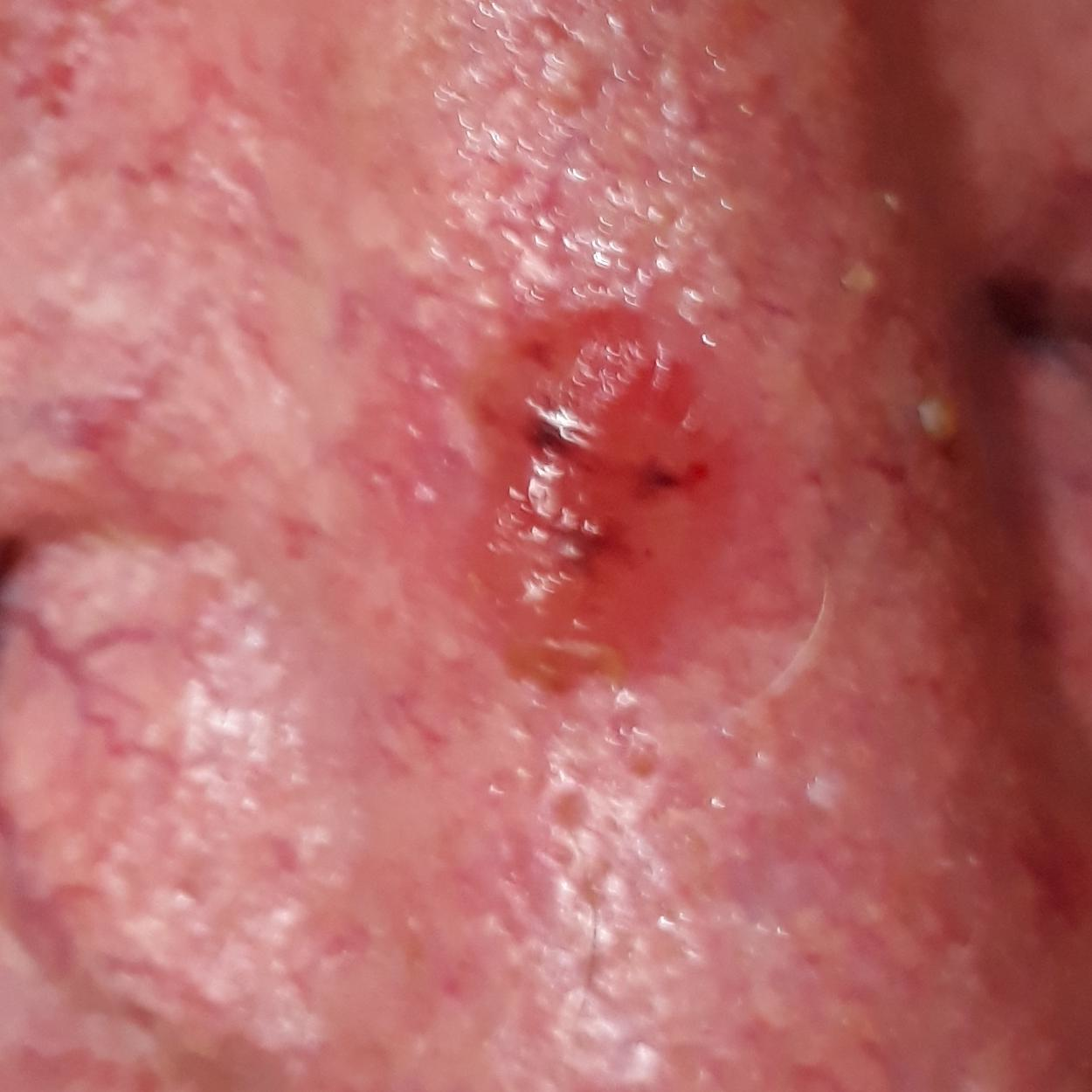anatomic site: the nose | symptoms: bleeding, itching, elevation | diagnosis: basal cell carcinoma (biopsy-proven).